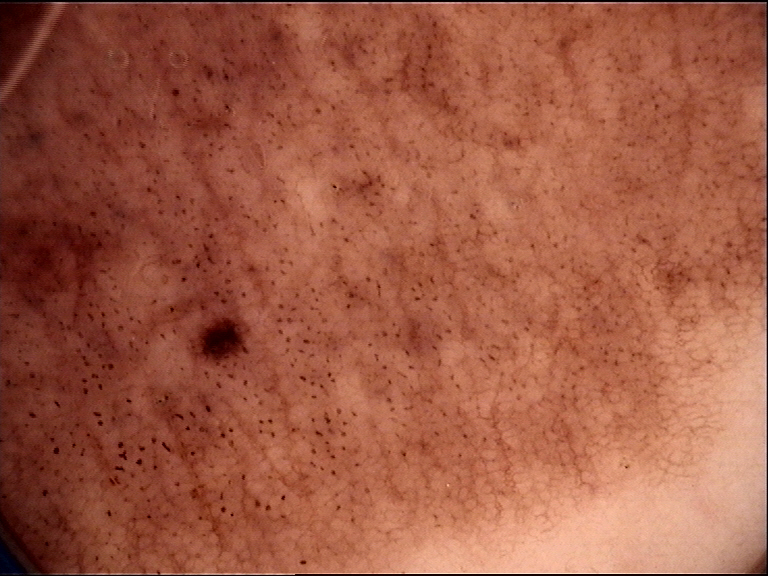Findings:
– image: dermoscopy
– classification: banal
– class: congenital junctional nevus (expert consensus)